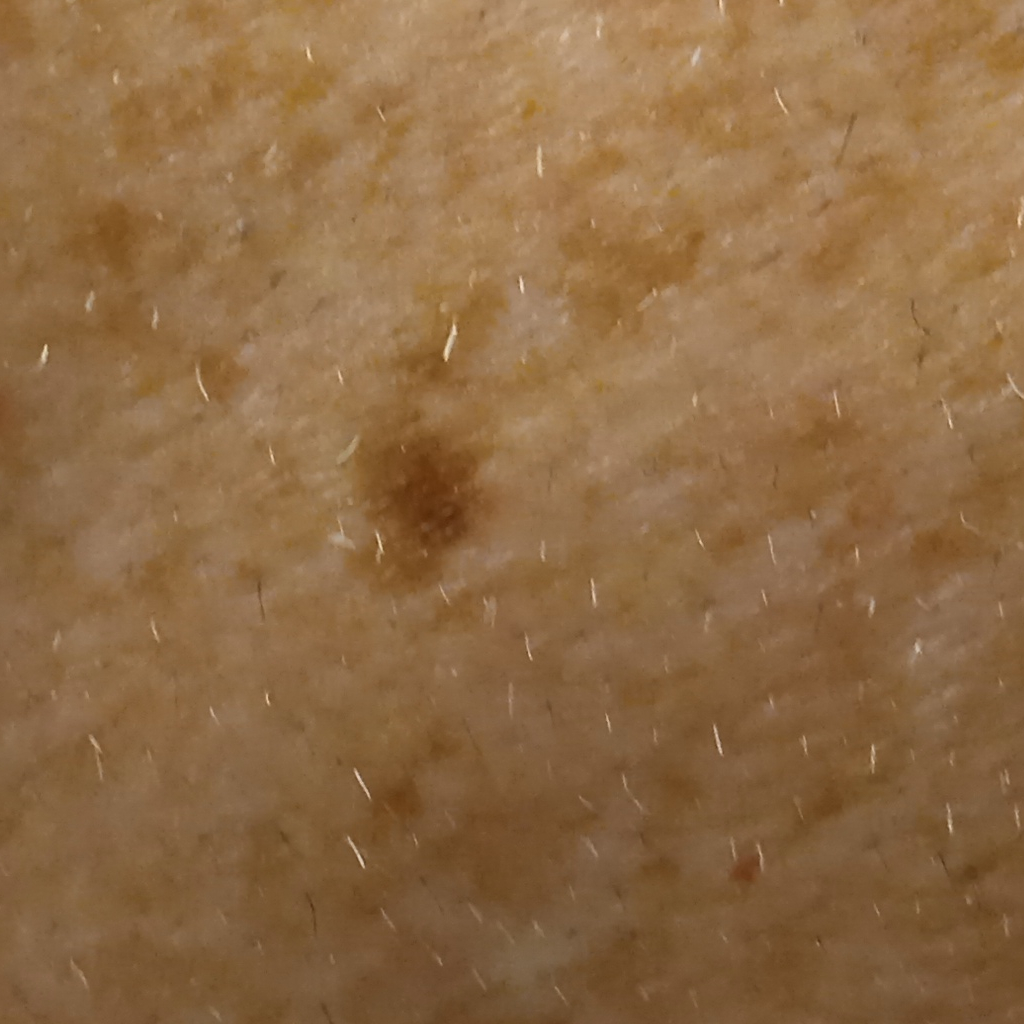The patient describes having numerous moles. By self-report, a personal history of cancer. The patient says their skin reddens with sun exposure. Collected as part of a research study, without a referral diagnosis. A male patient 73 years old. The lesion is on the torso. Measuring roughly 6.6 mm. The dermatologists' assessment was a melanoma.